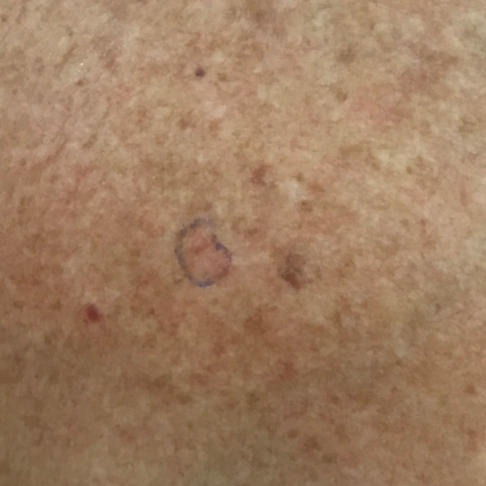Case summary:
A clinical photograph showing a skin lesion. A subject 41 years of age. By the patient's account, the lesion has not grown.
Conclusion:
Consistent with an actinic keratosis.